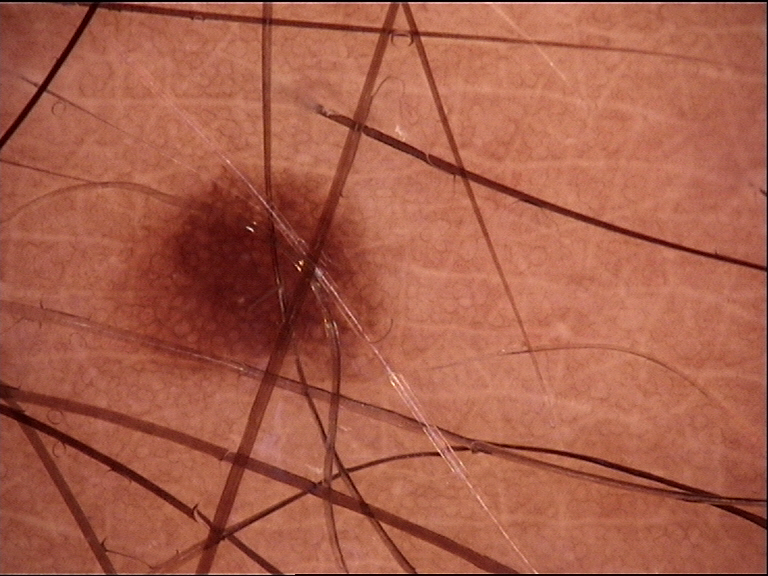{"diagnosis": {"name": "junctional nevus", "code": "jb", "malignancy": "benign", "super_class": "melanocytic", "confirmation": "expert consensus"}}